A patient in their 60s: 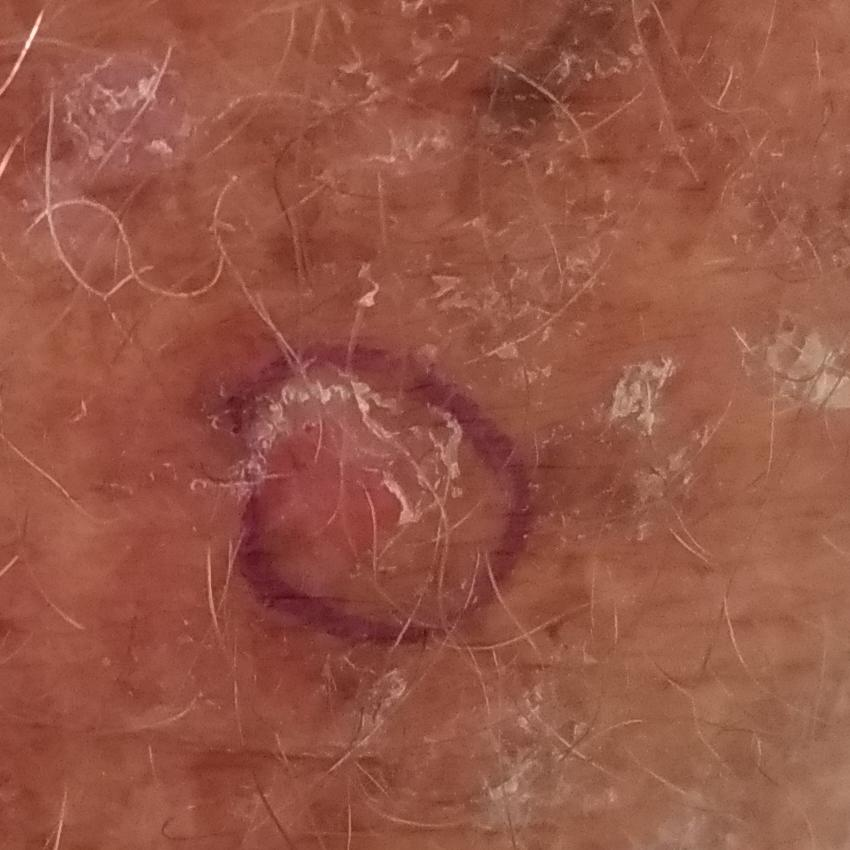Summary: Located on a forearm. The patient describes that the lesion is elevated and itches, but has not bled. Conclusion: The clinical impression was an actinic keratosis.